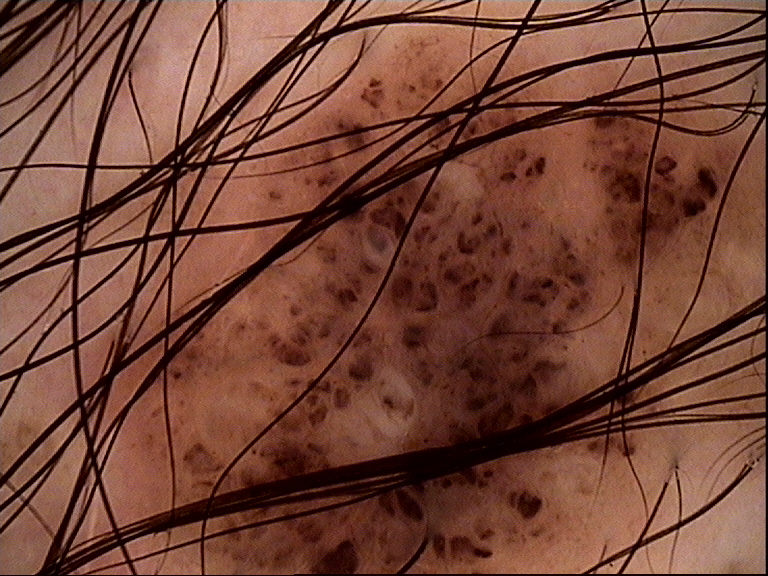Impression:
The diagnostic label was a compound nevus.